Male contributor, age 30–39; symptoms reported: itching, bothersome appearance and enlargement; the photograph was taken at an angle; the patient described the issue as a rash; located on the arm and leg; the patient notes the condition has been present for one to four weeks.
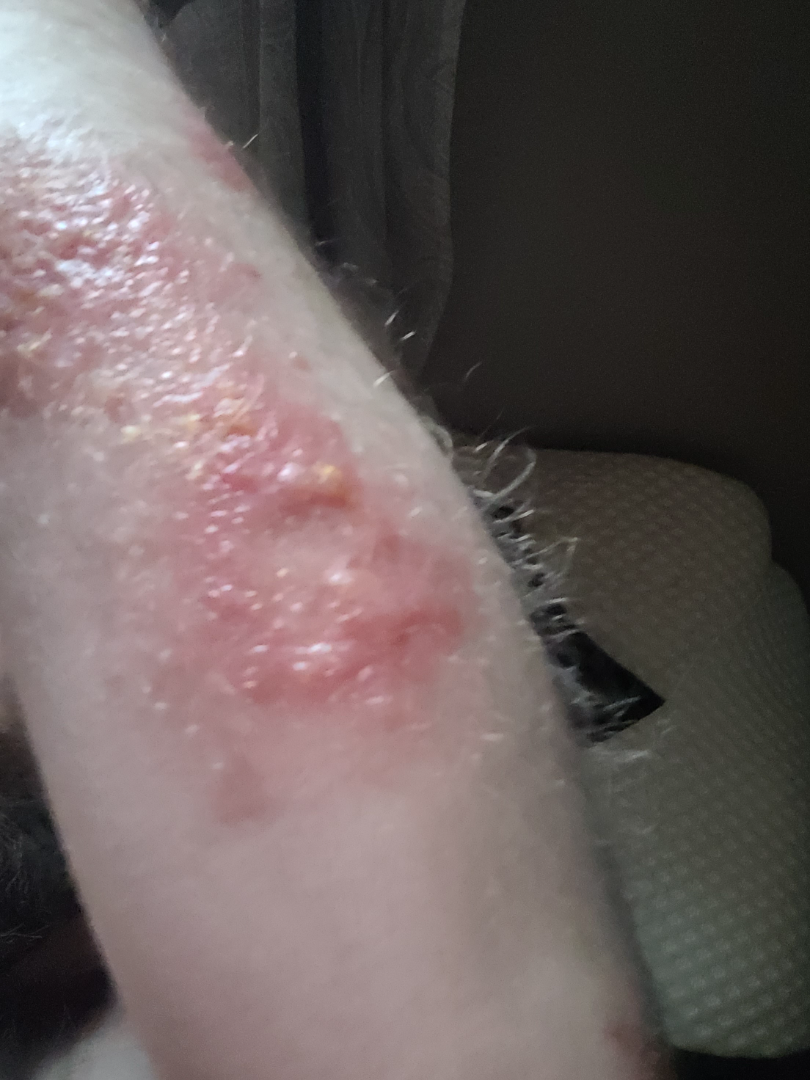Impression: The skin condition could not be confidently assessed from this image.